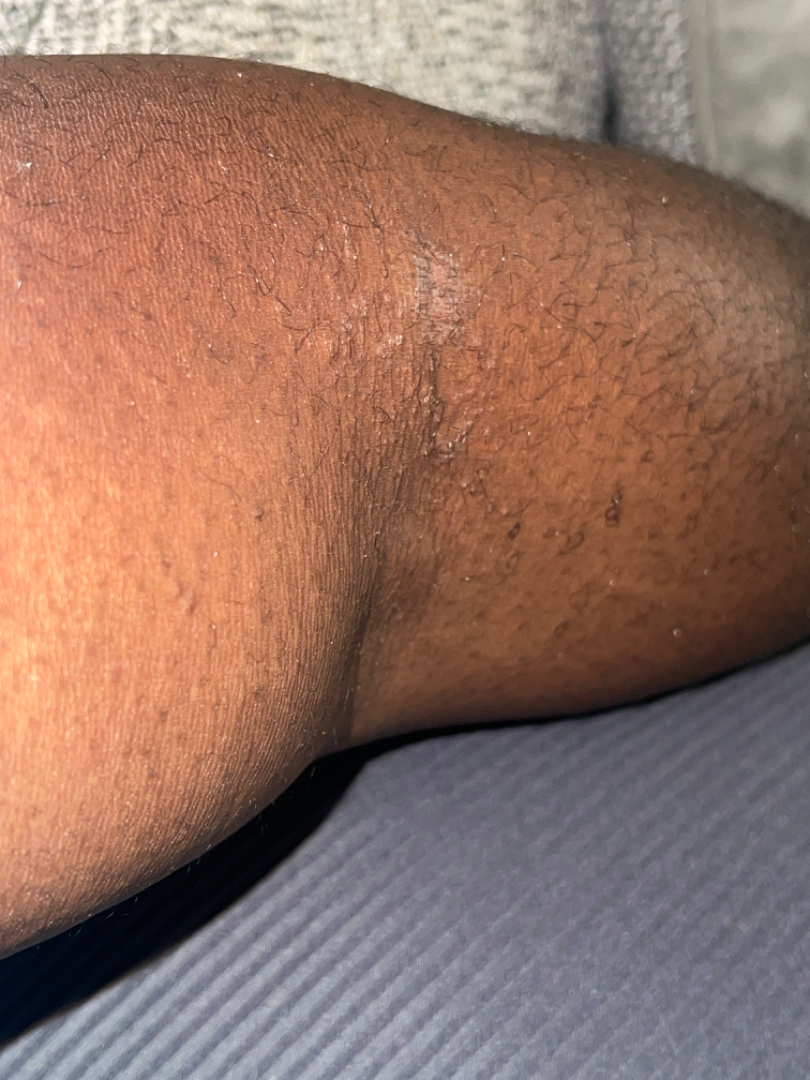Q: Anatomic location?
A: arm
Q: What is the framing?
A: at an angle
Q: What conditions are considered?
A: Eczema (1.00)